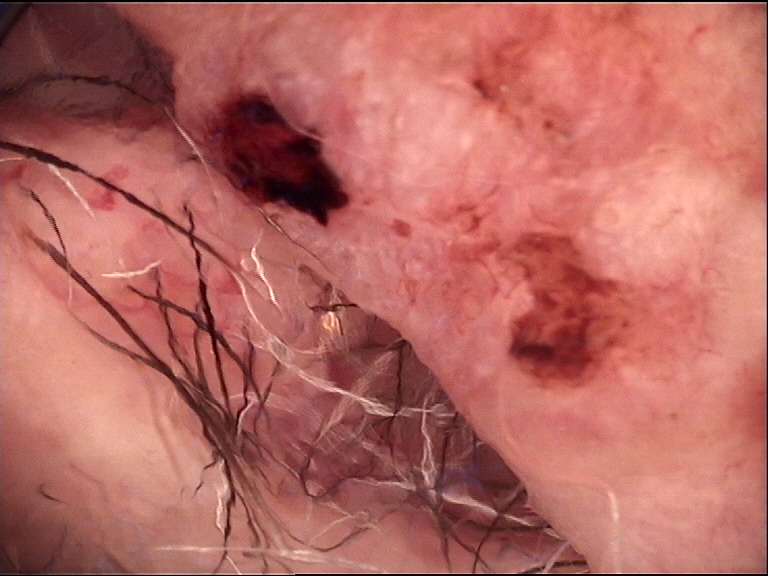A skin lesion imaged with a dermatoscope. Histopathology confirmed a keratinocytic, malignant lesion — a basal cell carcinoma.